A clinical photo of a skin lesion taken with a smartphone — 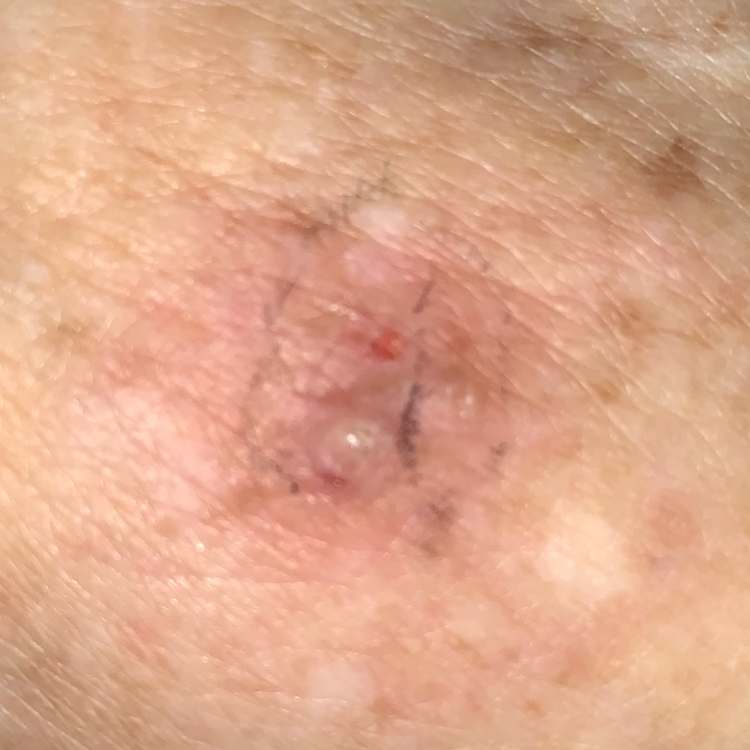Located on a forearm. By the patient's account, the lesion has not bled. On biopsy, the diagnosis was an actinic keratosis.